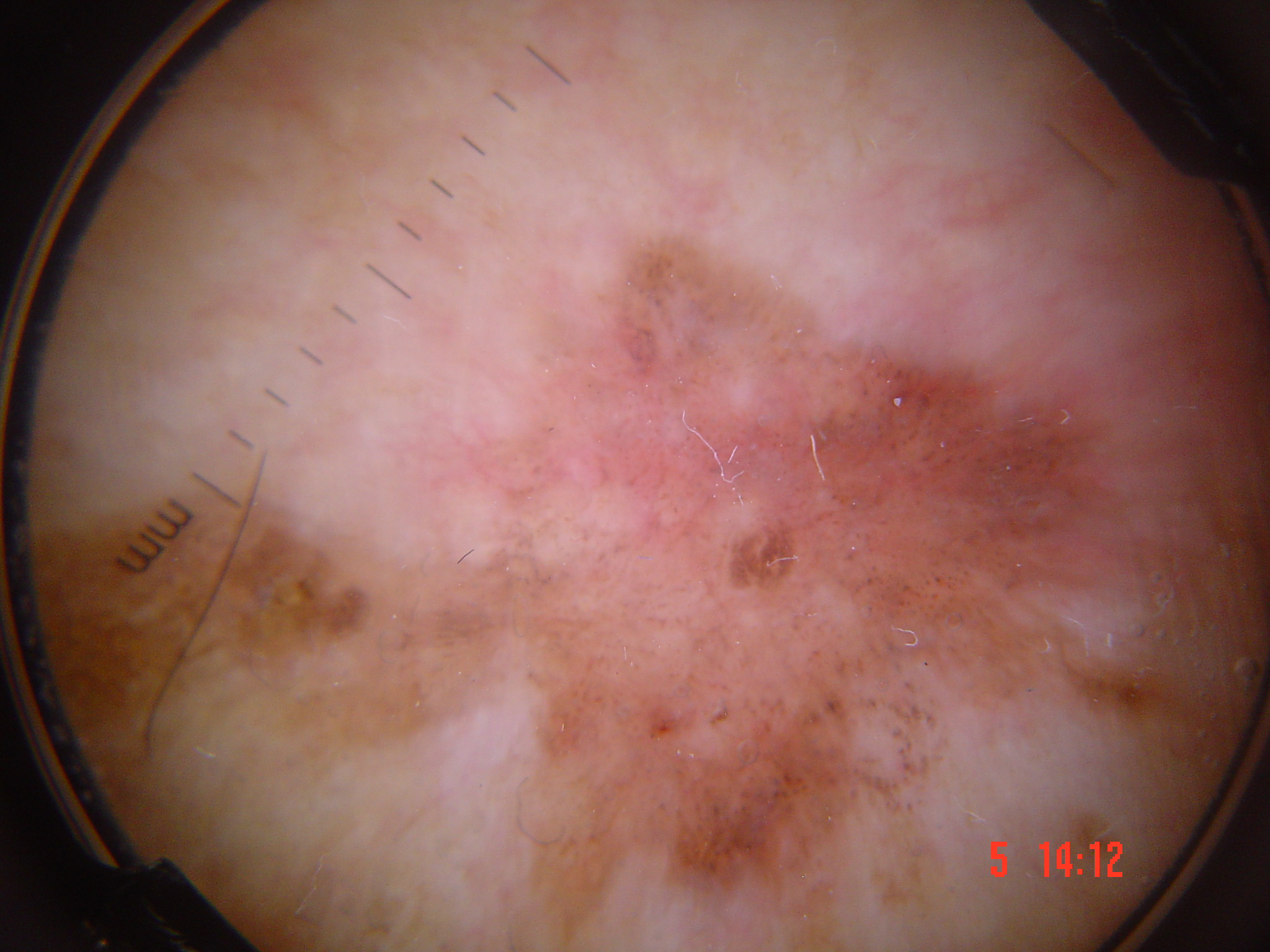Case:
• image type: dermatoscopy
• classification: keratinocytic
• pathology: Bowen's disease (biopsy-proven)